A dermatoscopic image of a skin lesion:
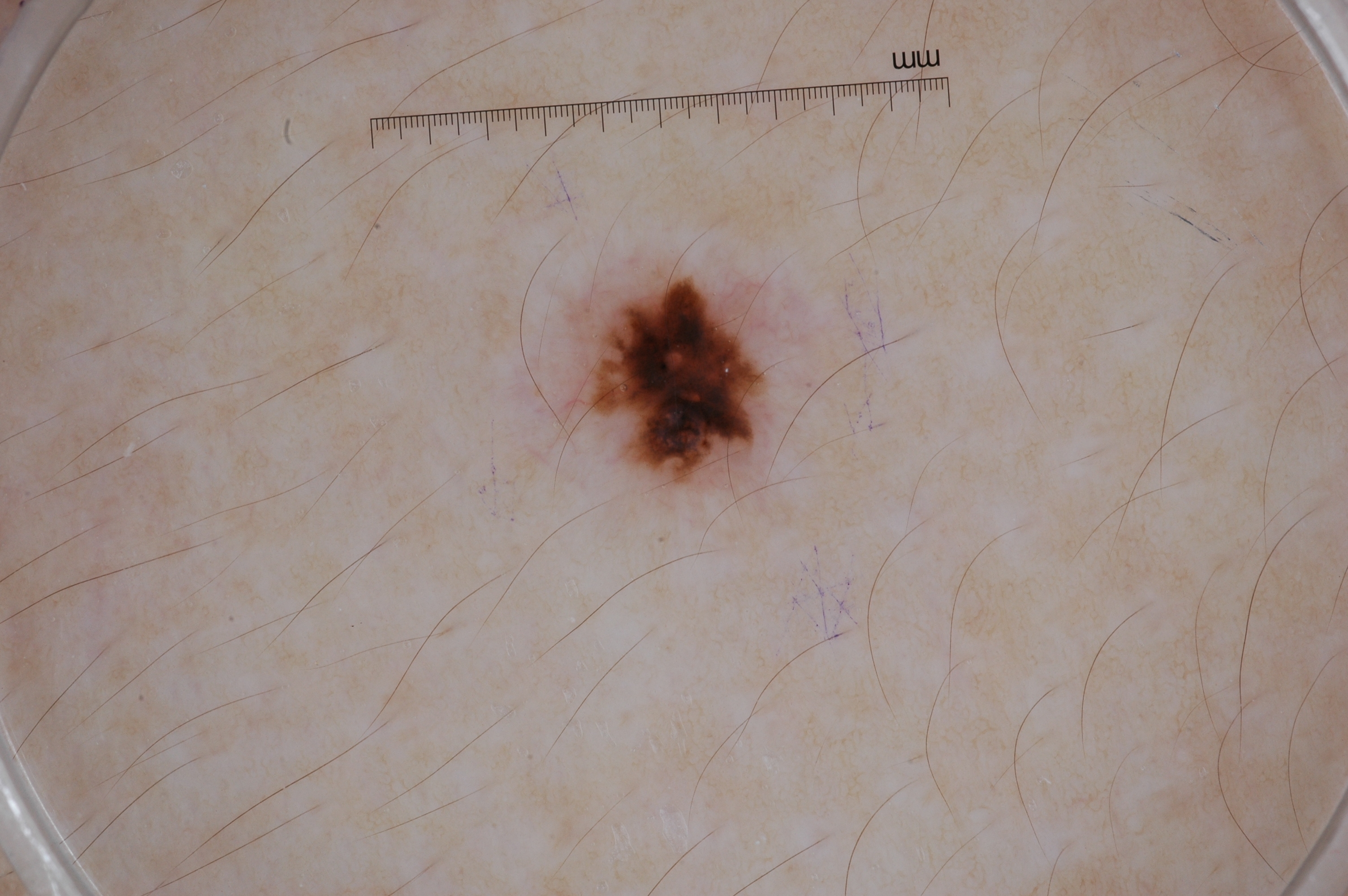Findings:
In (x1, y1, x2, y2) order, the lesion is bounded by <bbox>579, 280, 758, 483</bbox>.
Pathology:
On biopsy, the diagnosis was a melanoma.